A dermatoscopic image of a skin lesion. A male subject aged 38 to 42.
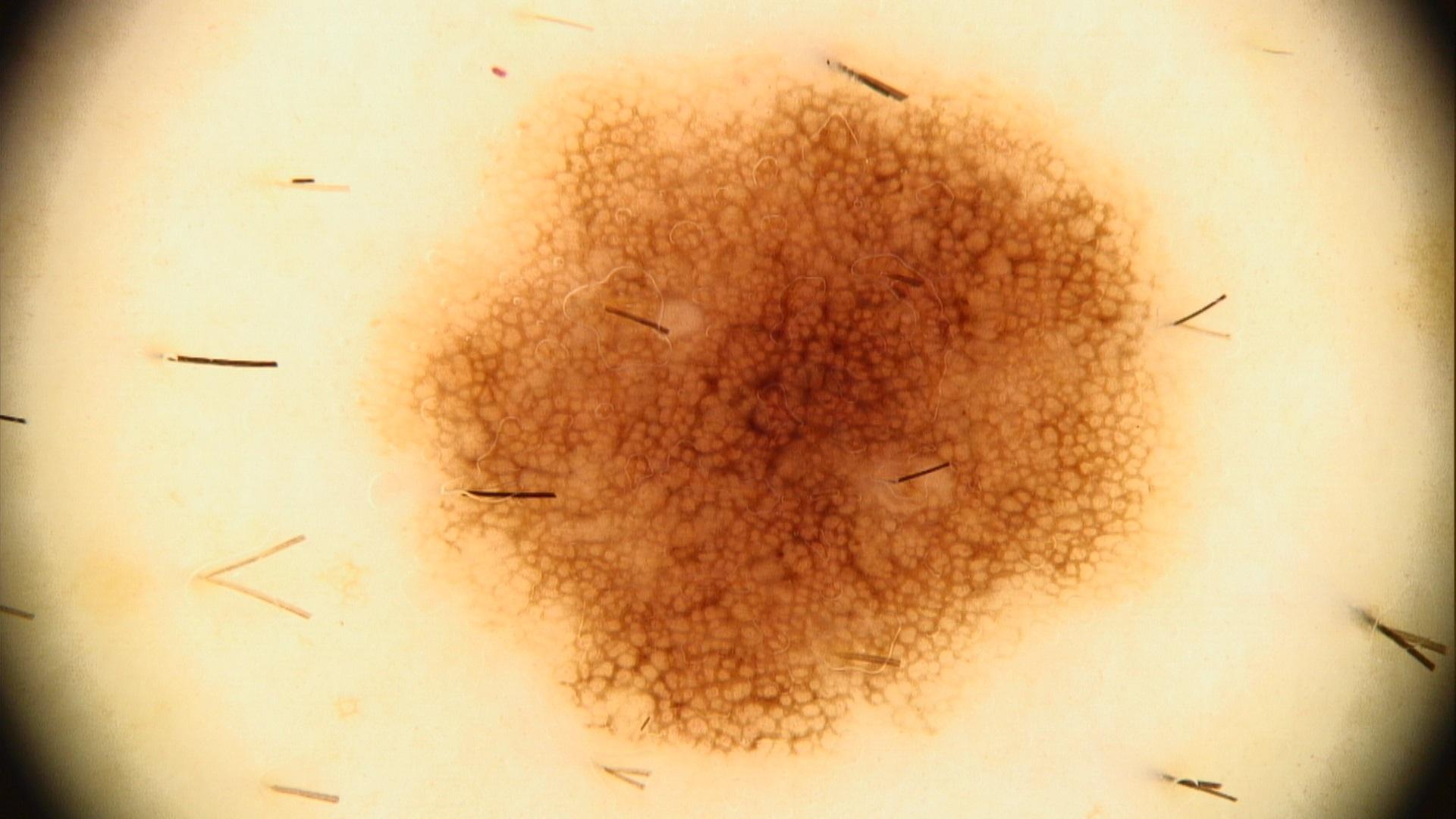Case:
* body site · an upper extremity
* impression · Nevus